A close-up photograph, skin tone: Fitzpatrick IV — 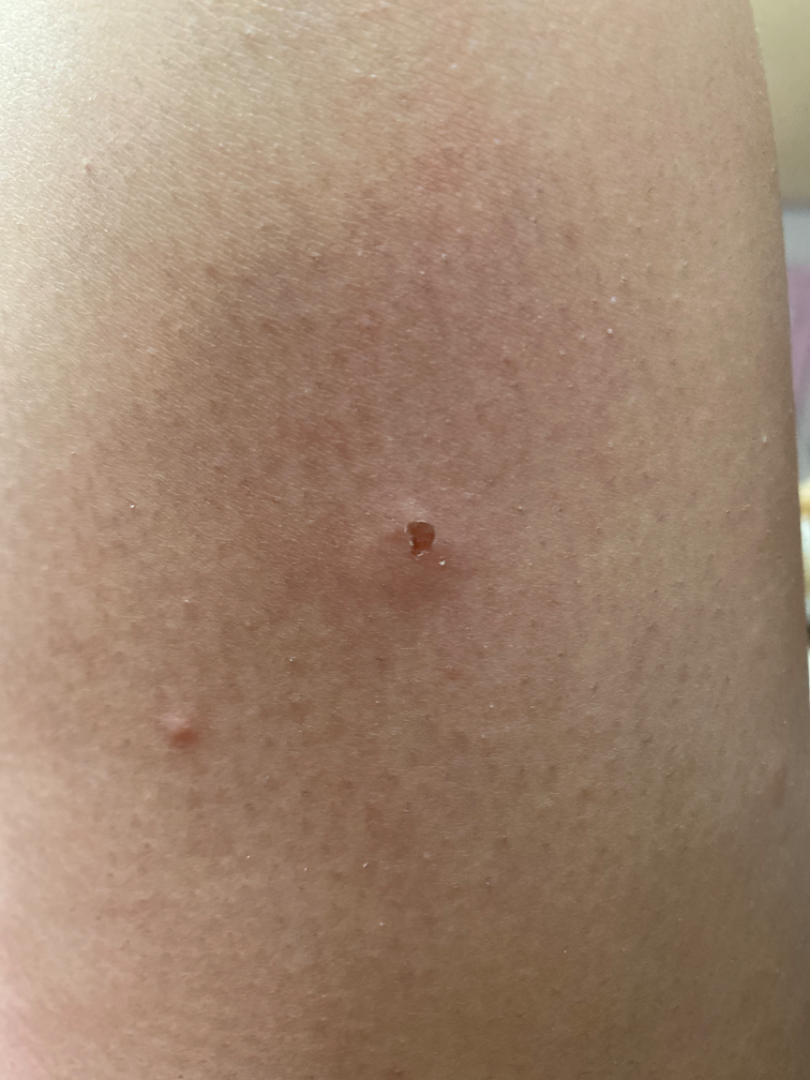assessment: ungradable on photographic review